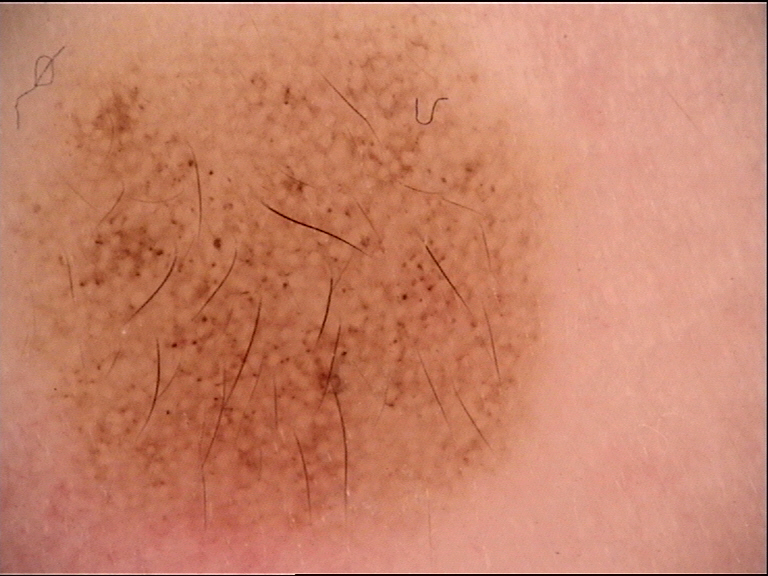Case:
– label — congenital junctional nevus (expert consensus)